This image was taken at an angle · the lesion is described as flat and rough or flaky · the patient is female · the affected area is the arm — 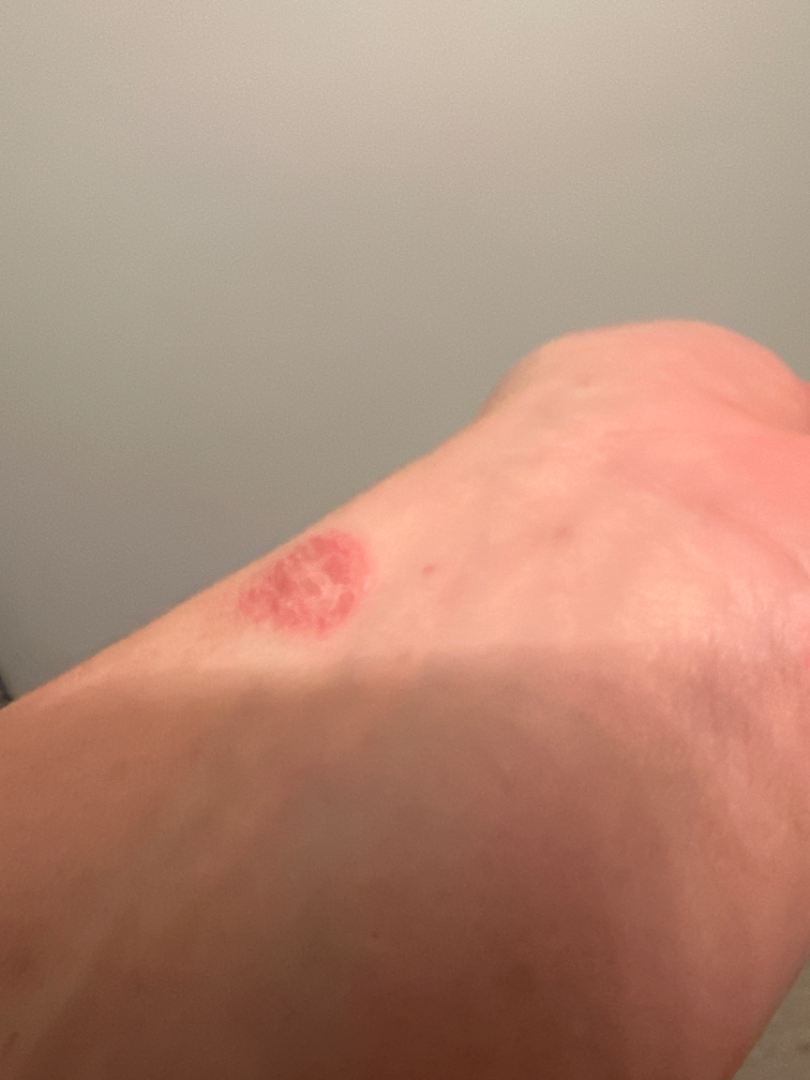On photographic review, most consistent with Allergic Contact Dermatitis; the differential also includes Irritant Contact Dermatitis.